A female patient about 10 years old, this is a dermoscopic photograph of a skin lesion: 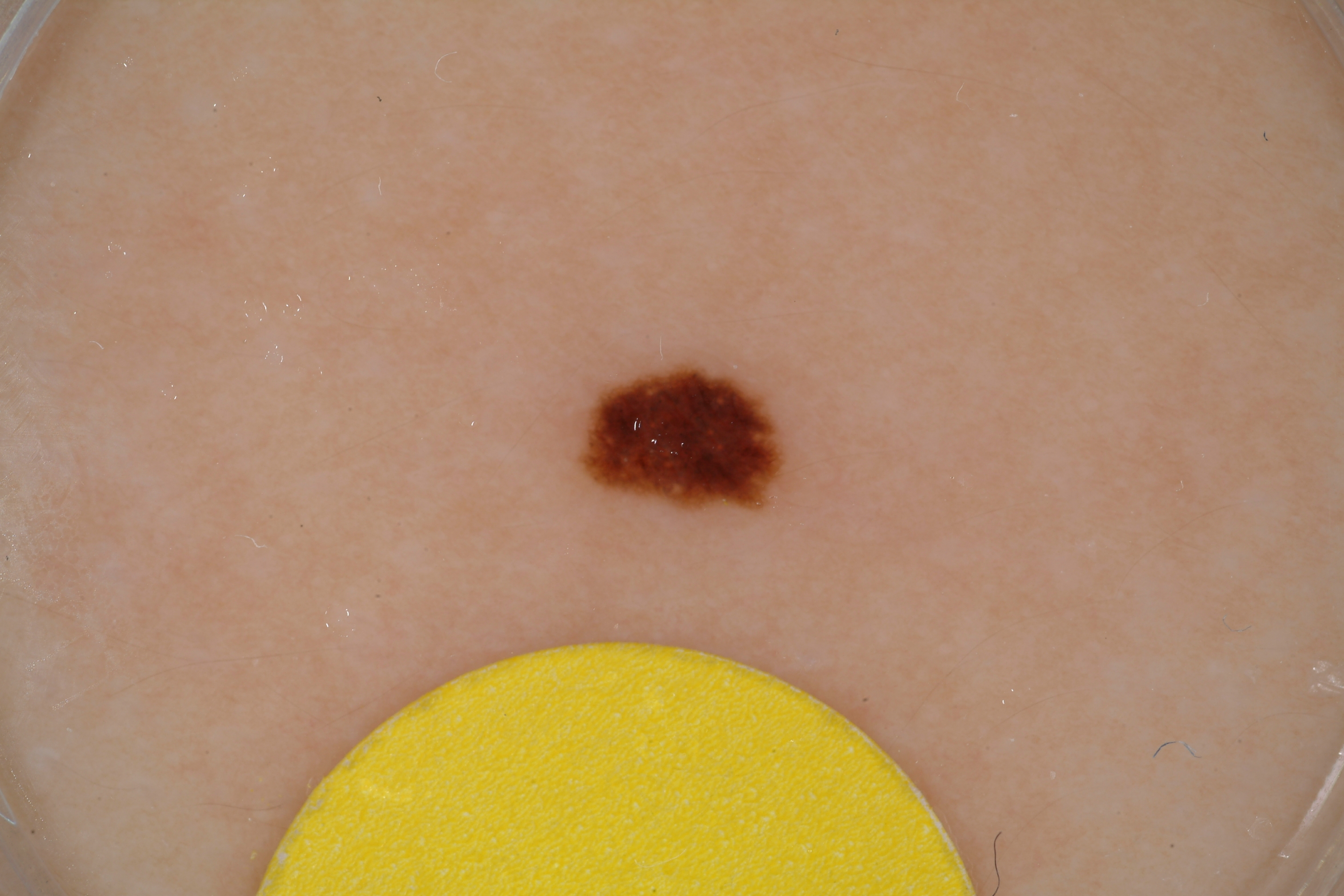<case>
<lesion_location>
  <bbox_xyxy>574, 360, 793, 516</bbox_xyxy>
</lesion_location>
<dermoscopic_features>
  <present/>
  <absent>milia-like cysts, streaks, negative network, pigment network</absent>
</dermoscopic_features>
<diagnosis>
  <name>melanocytic nevus</name>
  <malignancy>benign</malignancy>
  <lineage>melanocytic</lineage>
  <provenance>clinical</provenance>
</diagnosis>
</case>